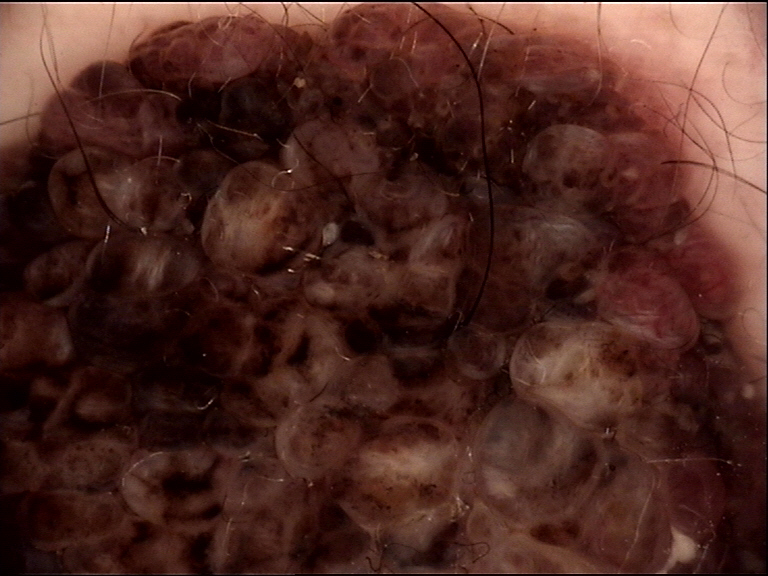Q: What is the diagnosis?
A: congenital compound nevus (expert consensus)